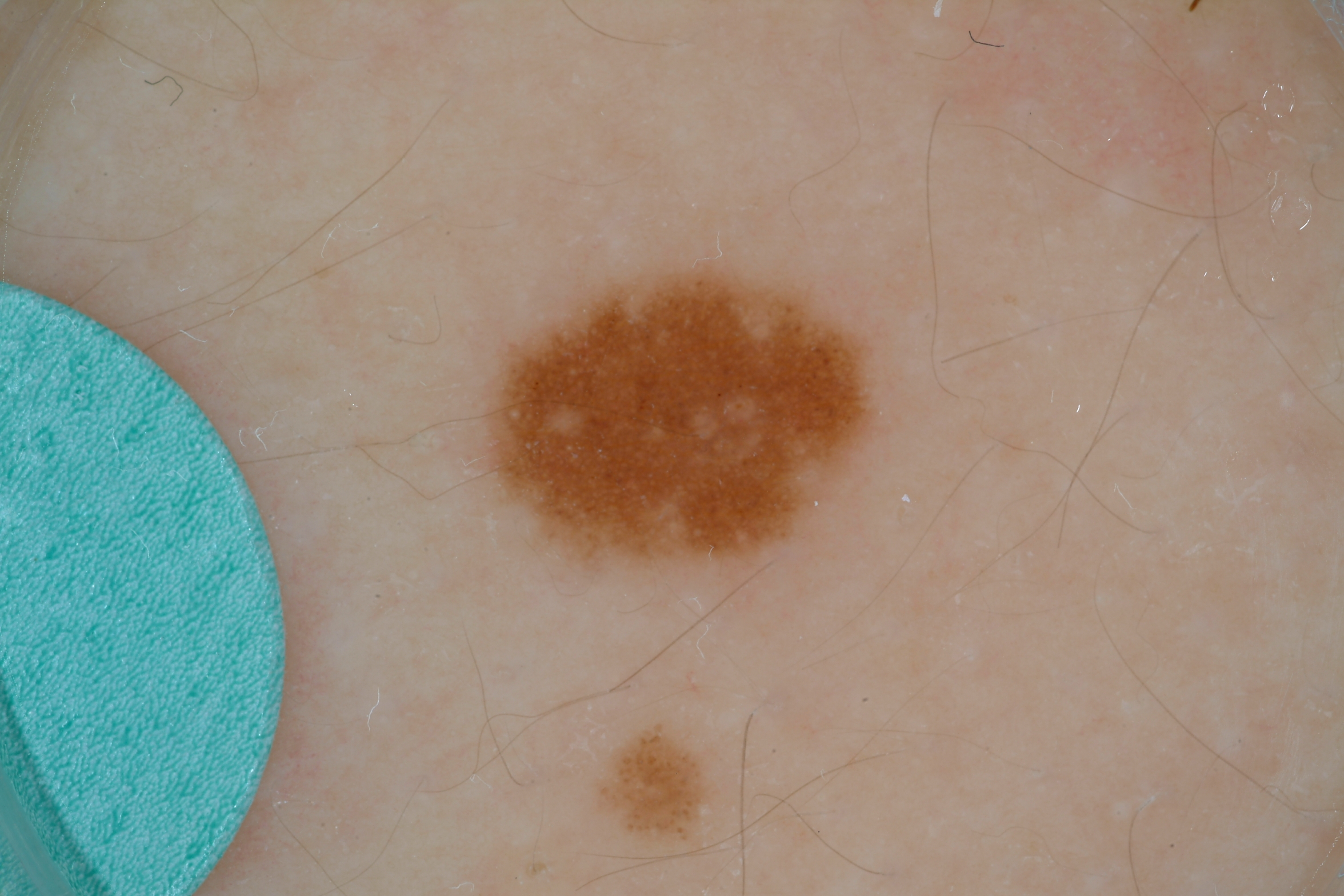Image and clinical context: A dermoscopic close-up of a skin lesion. In (x1, y1, x2, y2) order, the visible lesion spans 481, 261, 883, 579. Dermoscopic examination shows globules, pigment network, and milia-like cysts, with no streaks or negative network. Conclusion: The diagnostic assessment was a melanocytic nevus, a benign lesion.